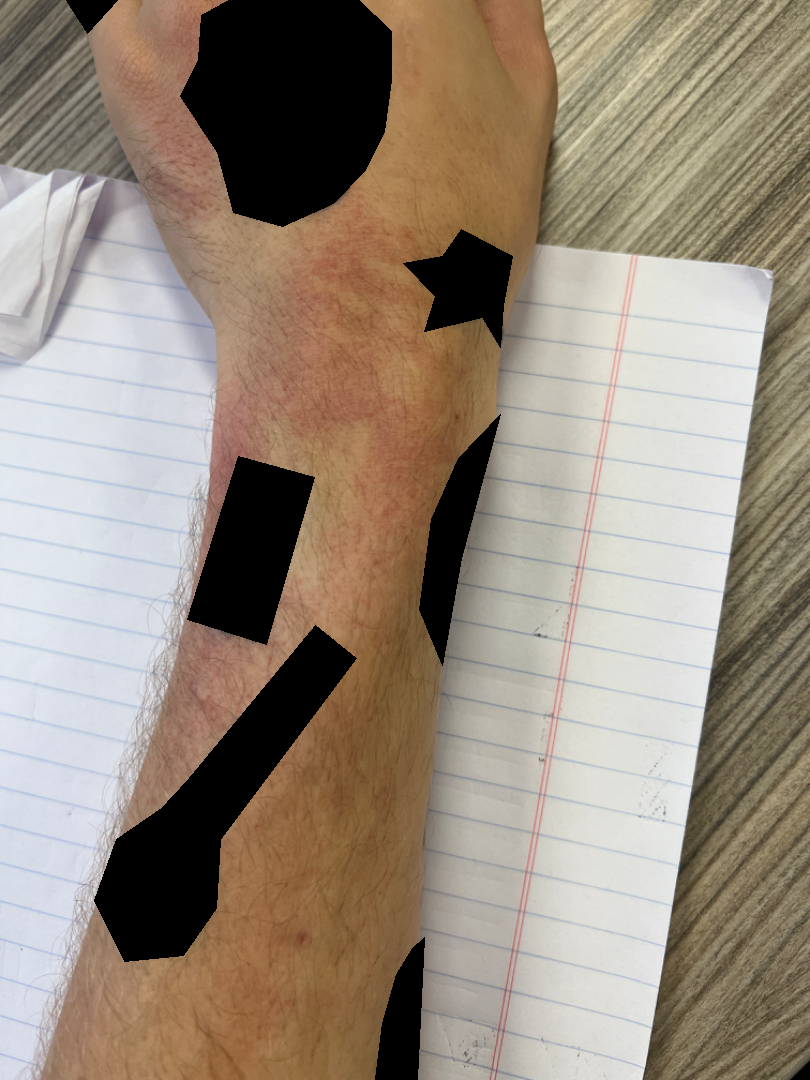Q: Who is the patient?
A: male
Q: What is the framing?
A: close-up
Q: What is the affected area?
A: arm and back of the hand
Q: What conditions are considered?
A: most consistent with Allergic Contact Dermatitis